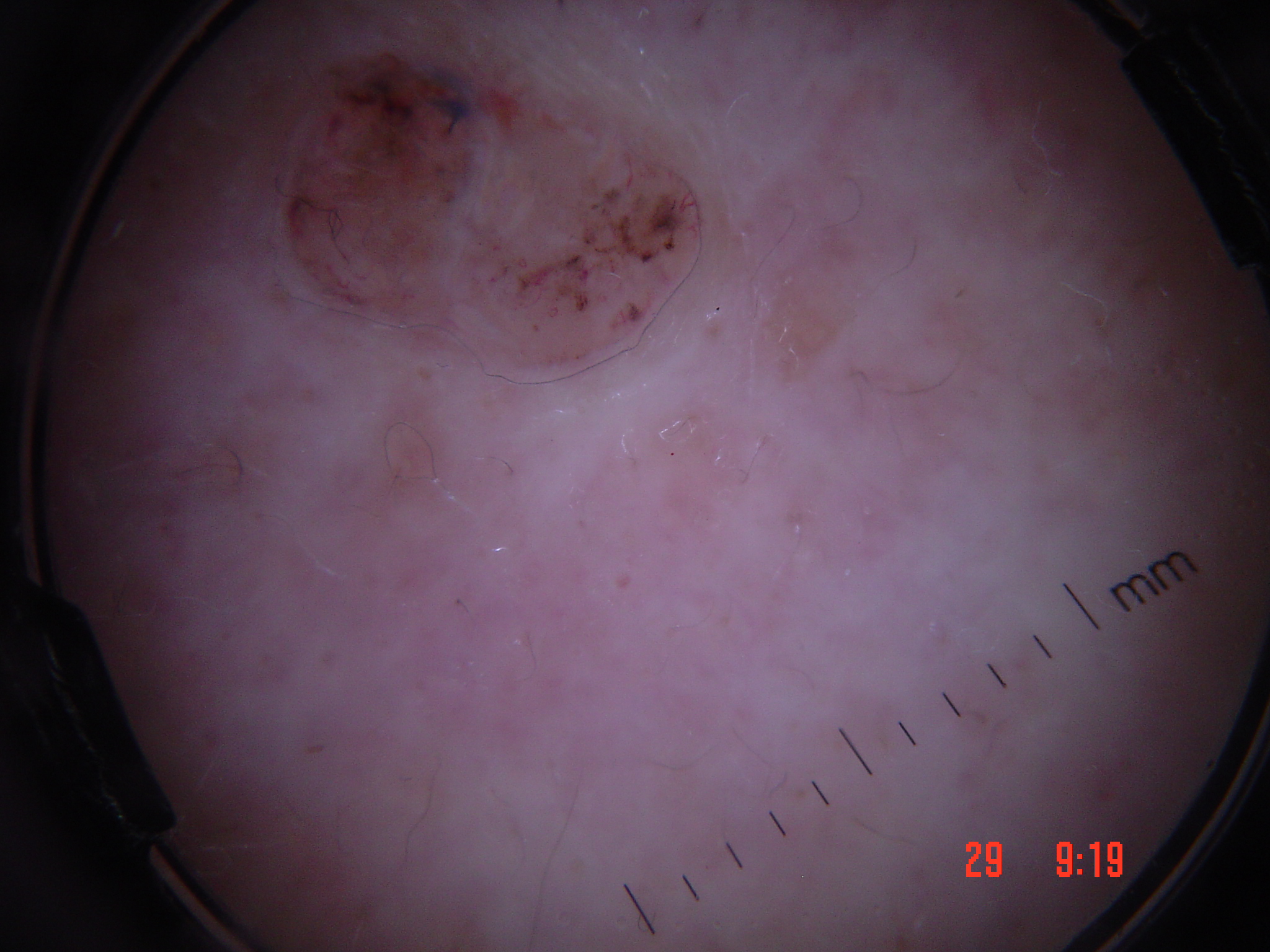Conclusion: Histopathology confirmed a basal cell carcinoma.